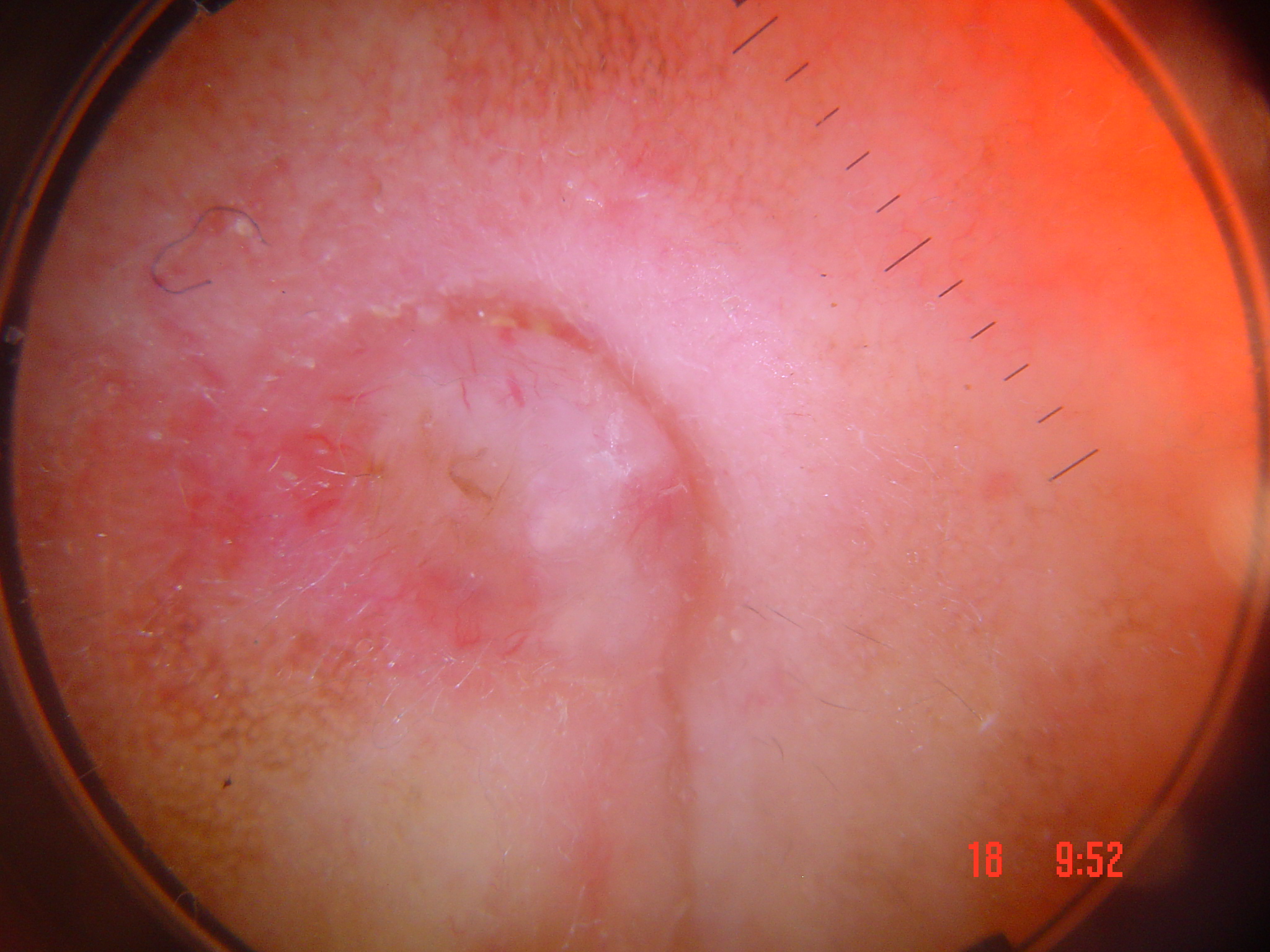A dermoscopic image of a skin lesion.
The biopsy diagnosis was a keratinocytic lesion — a basal cell carcinoma.